A close-up photograph. The head or neck is involved. The subject is a female aged 18–29.
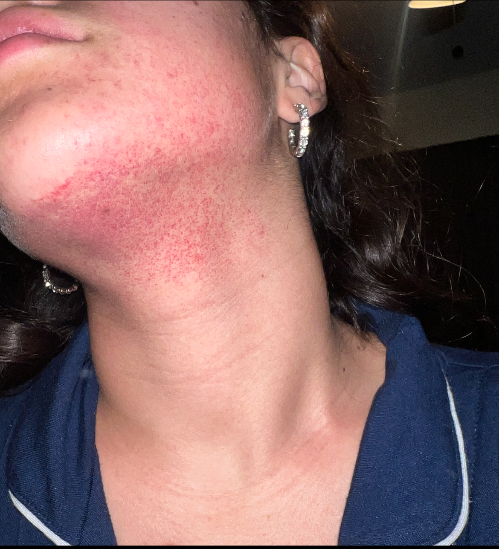Assessment: The condition could not be reliably identified from the image.